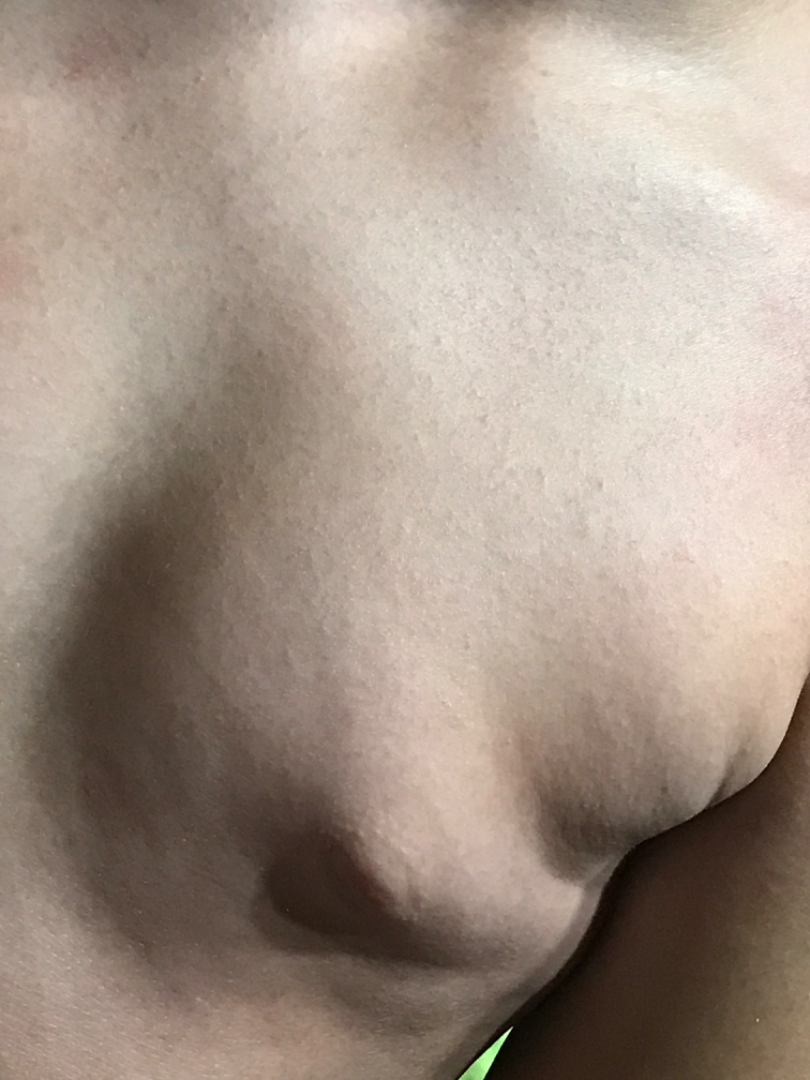Background: Present for about one day. Self-categorized by the patient as a rash. Texture is reported as raised or bumpy. Symptoms reported: bothersome appearance. The photograph was taken at an angle. The arm and head or neck are involved. Findings: The reviewing dermatologist's impression was: Miliaria and Folliculitis were considered with similar weight.